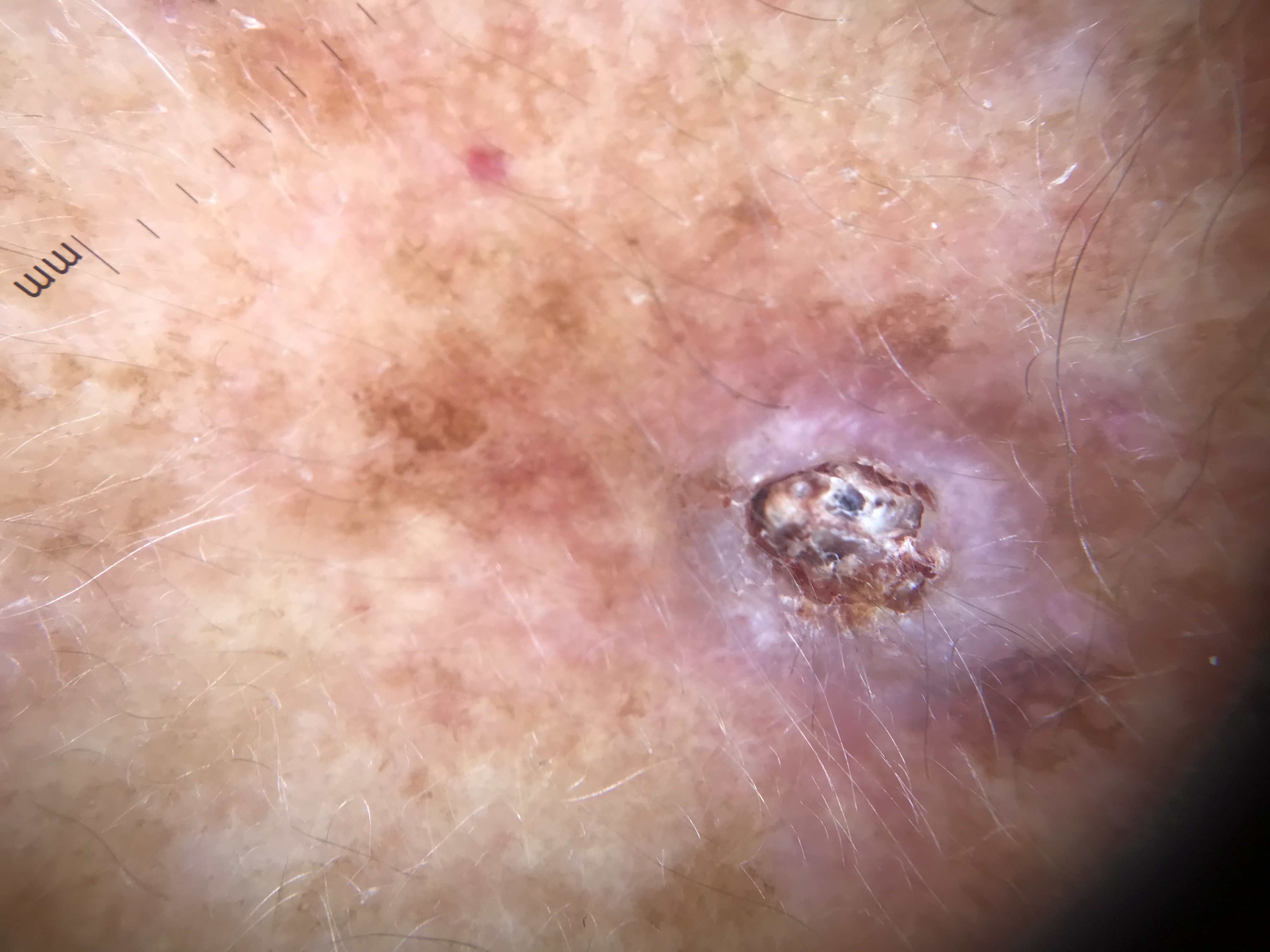diagnostic label: squamous cell carcinoma (biopsy-proven).